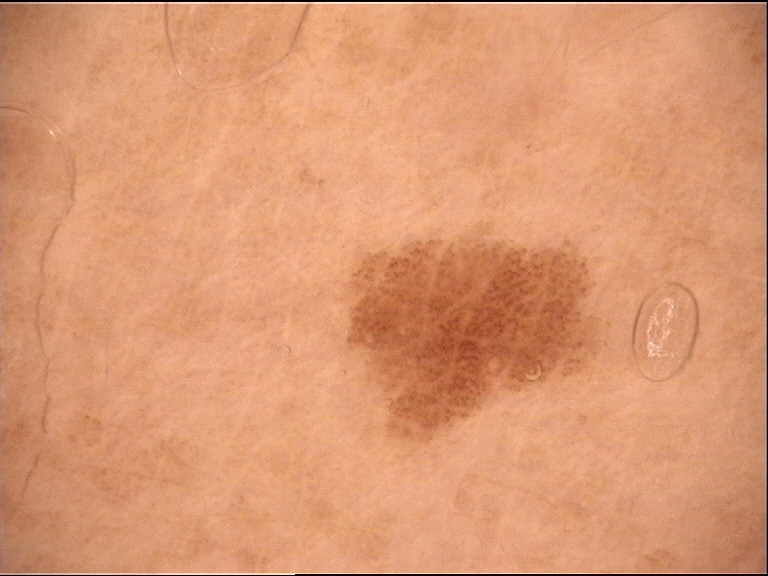assessment = junctional nevus (expert consensus)